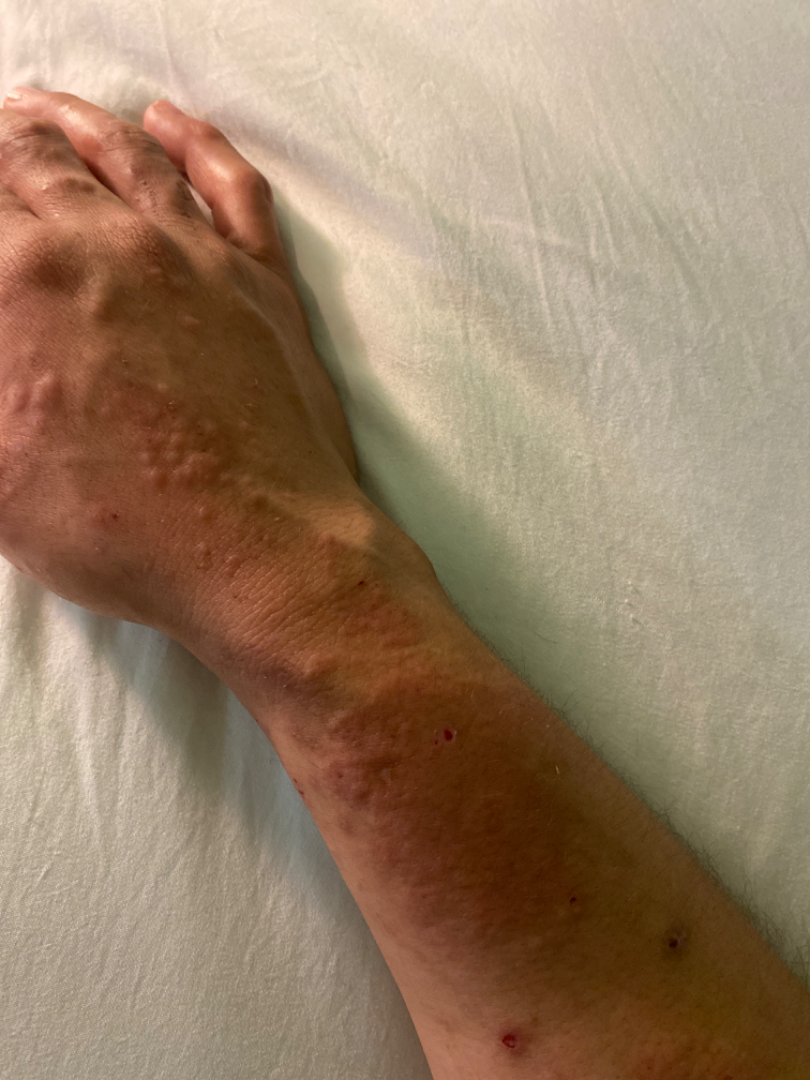– assessment: indeterminate from the photograph